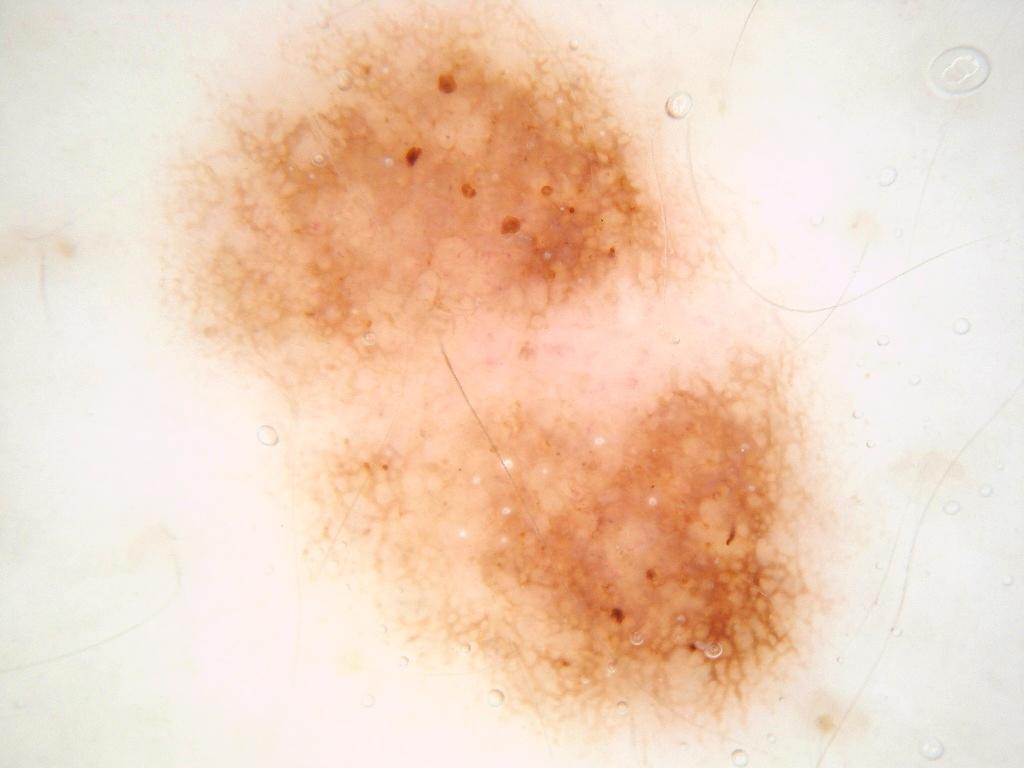• patient — female, in their mid-30s
• image — dermatoscopic image of a skin lesion
• dermoscopic findings — milia-like cysts, pigment network, and globules; absent: negative network and streaks
• location — [151, 0, 867, 749]
• impression — a melanocytic nevus, a benign skin lesion